A dermatoscopic image of a skin lesion.
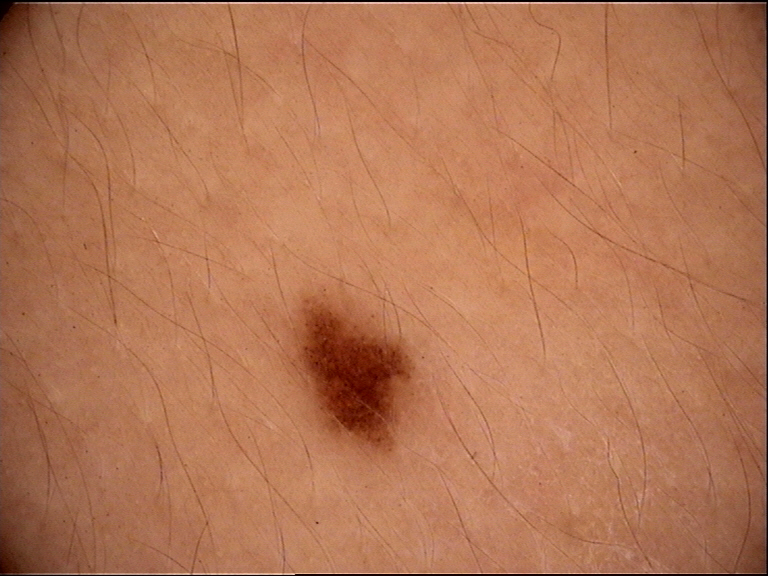Findings:
– classification · banal
– assessment · junctional nevus (expert consensus)